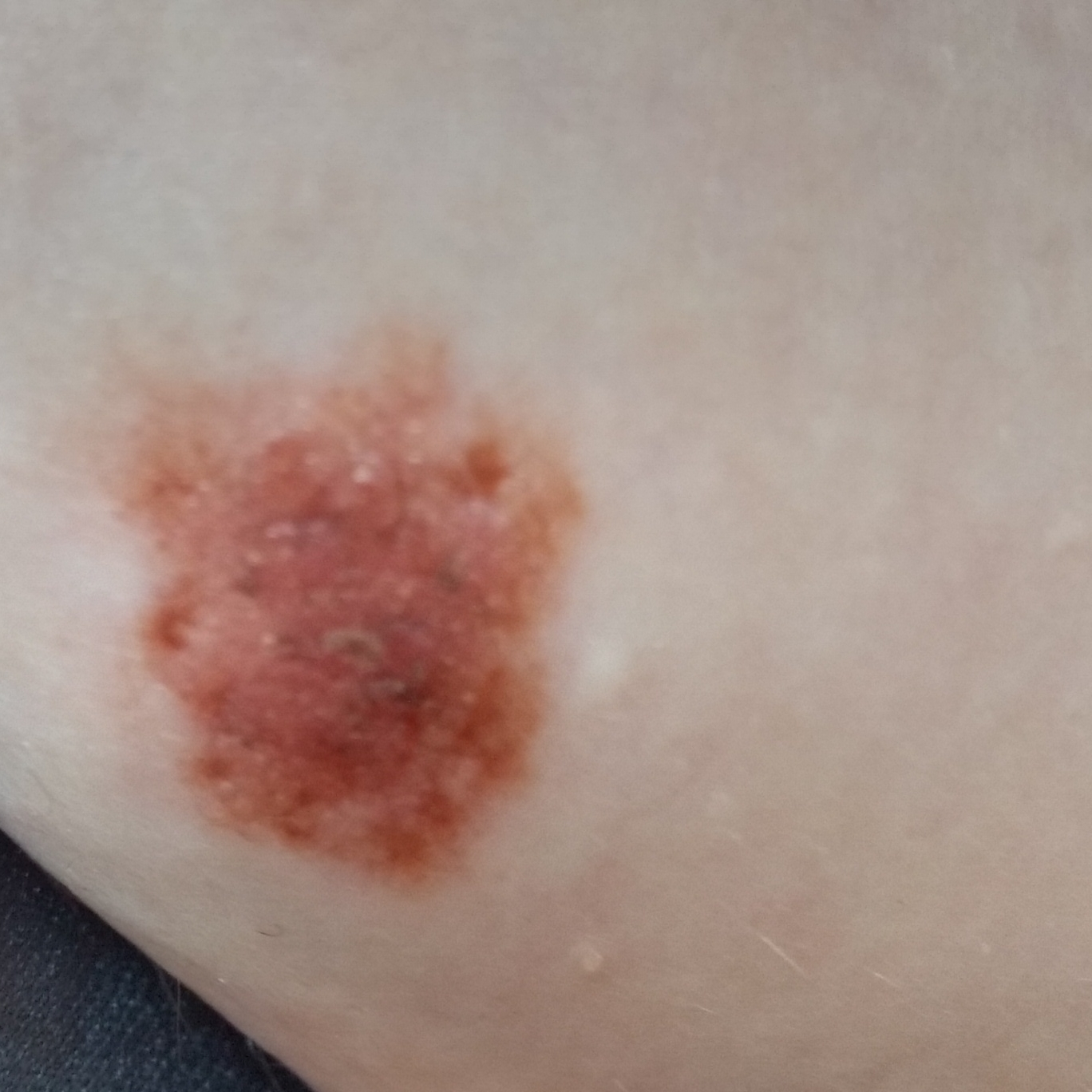modality = clinical photo; subject = 17 years old; location = the chest; patient-reported symptoms = growth, elevation; assessment = nevus (clinical consensus).